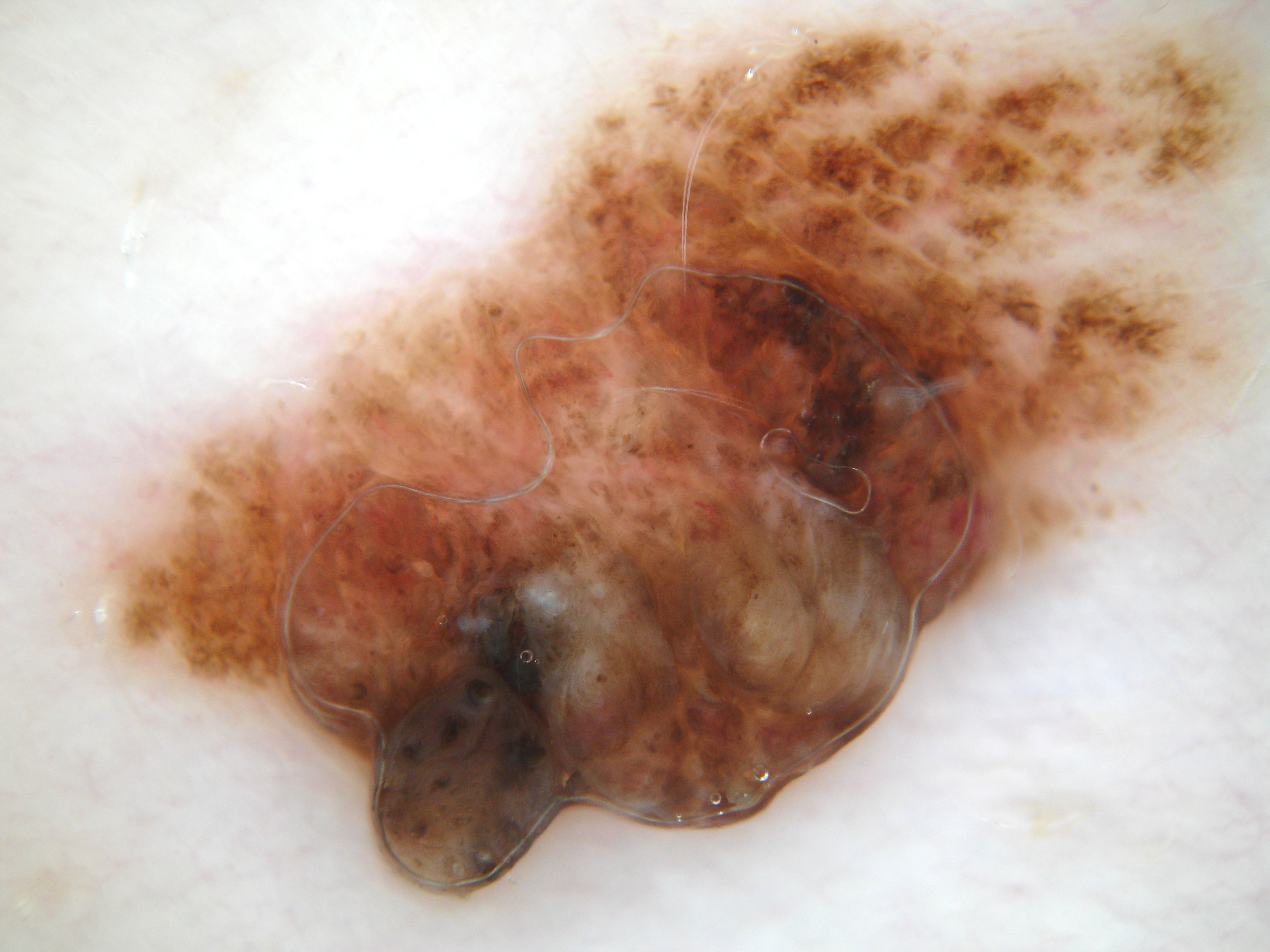Findings:
Dermoscopy of a skin lesion. As (left, top, right, bottom), lesion location: 60/3/1269/897. Dermoscopy demonstrates no milia-like cysts, negative network, streaks, globules, or pigment network.
Impression:
Clinically diagnosed as a melanocytic nevus, a benign lesion.